Dermoscopy of a skin lesion; the subject is a male roughly 45 years of age — 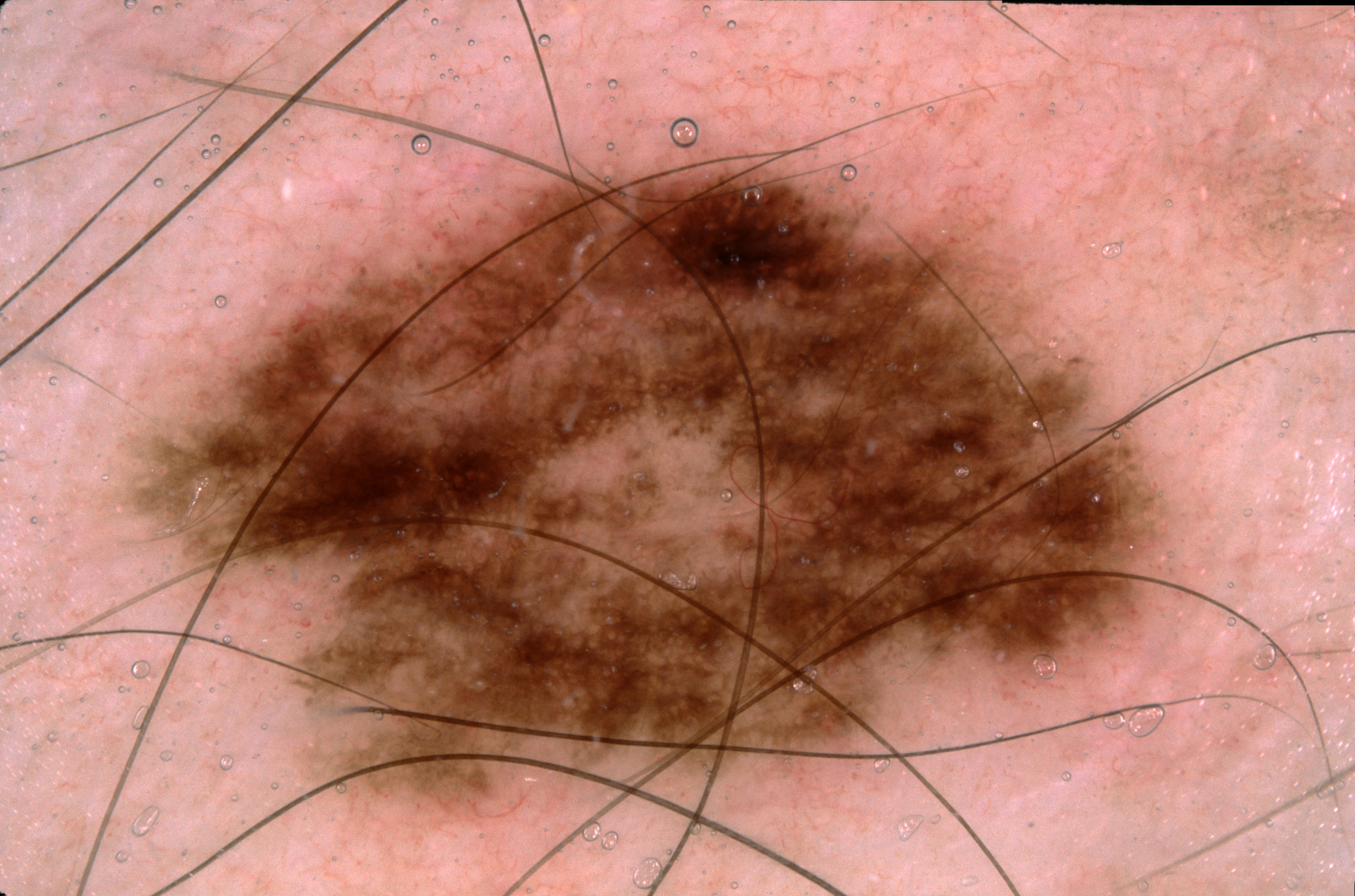Q: What does dermoscopy show?
A: pigment network; absent: milia-like cysts, negative network, and streaks
Q: How large is the lesion within the image?
A: ~38% of the field
Q: Where is the lesion in the image?
A: bbox=[148, 161, 1164, 819]
Q: What did the assessment conclude?
A: a melanocytic nevus